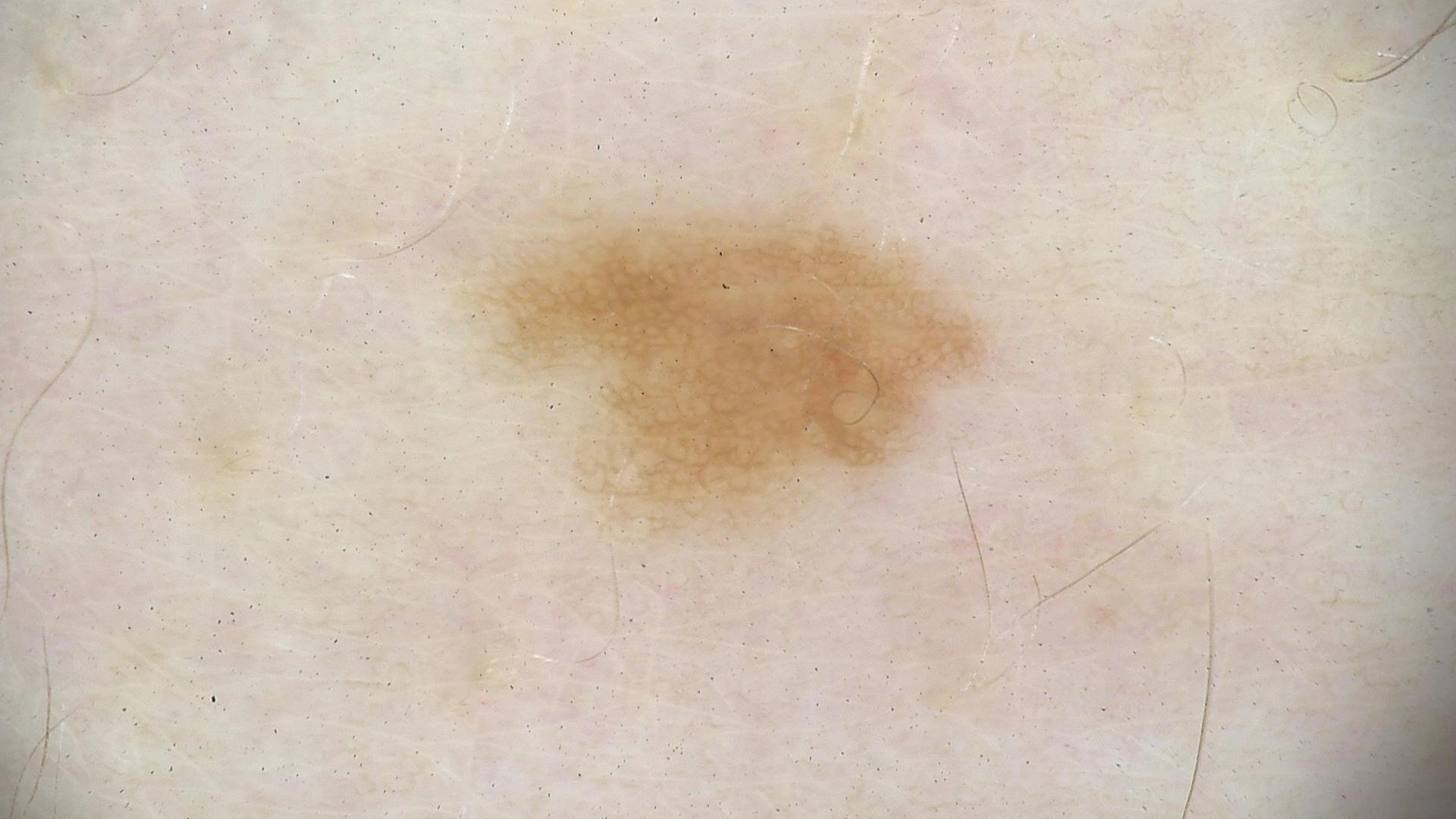Dermoscopy of a skin lesion.
Consistent with a dysplastic junctional nevus.